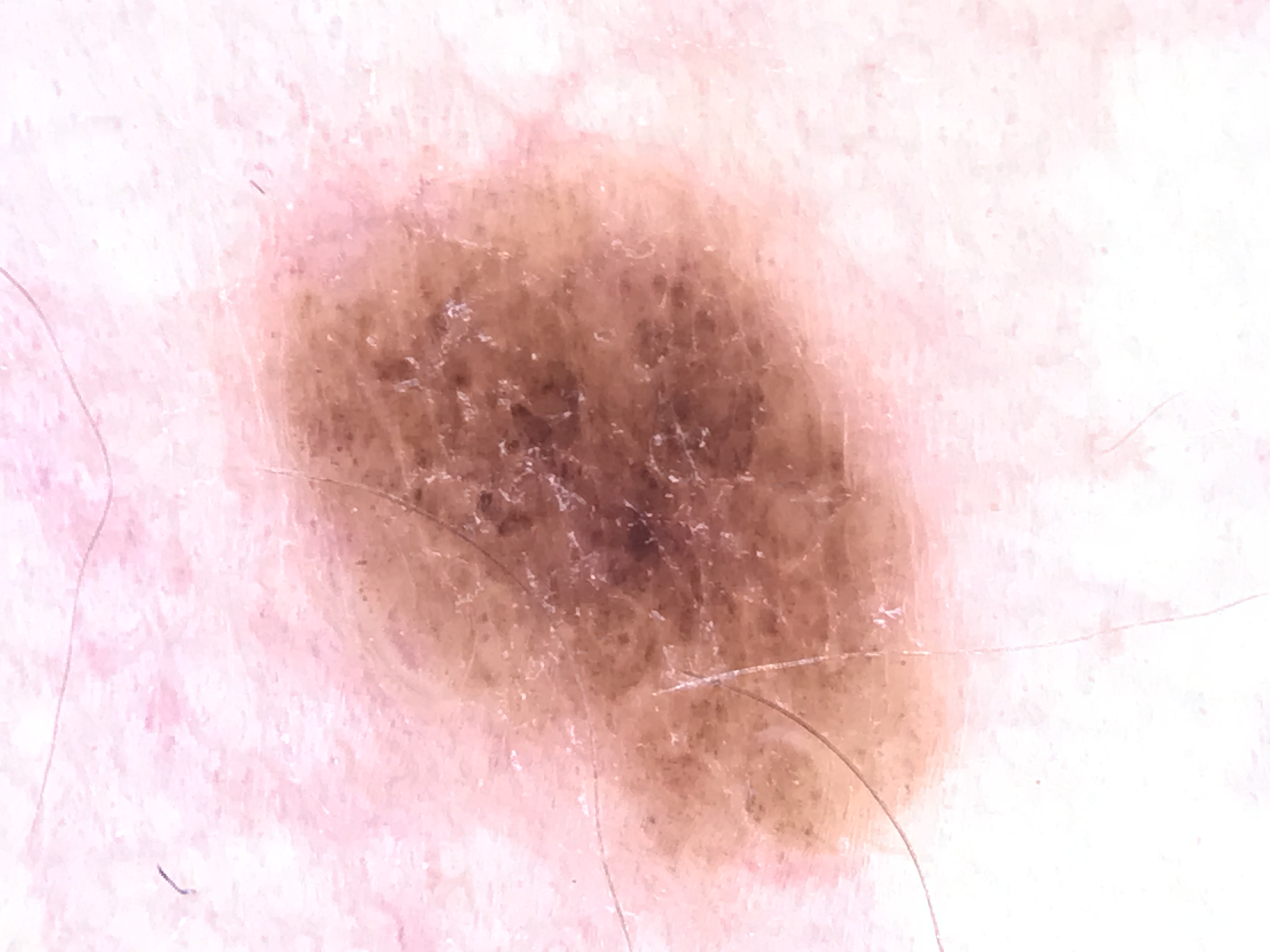<dermoscopy>
<diagnosis>
<name>dysplastic compound nevus</name>
<code>cd</code>
<malignancy>benign</malignancy>
<super_class>melanocytic</super_class>
<confirmation>expert consensus</confirmation>
</diagnosis>
</dermoscopy>